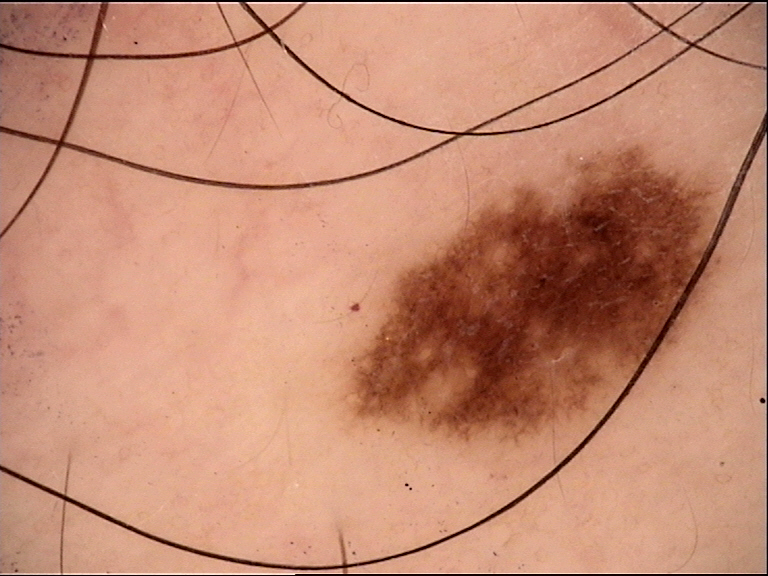diagnostic label: dysplastic junctional nevus (expert consensus).